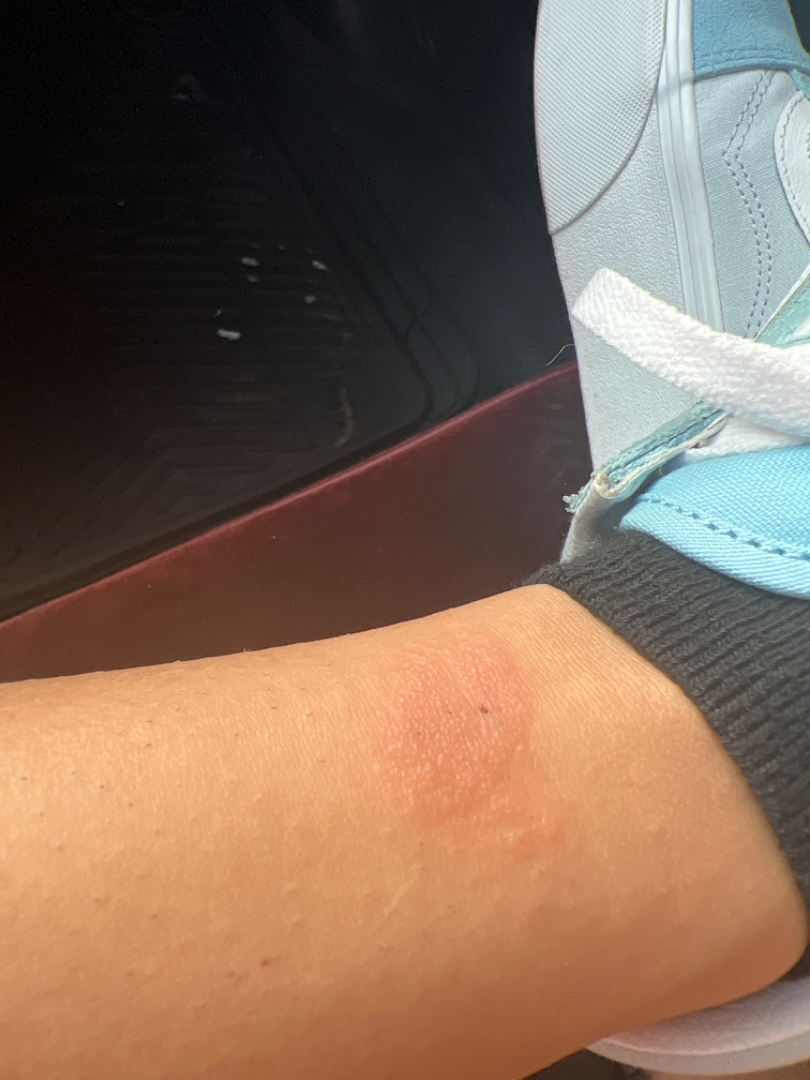image framing = at a distance, location = leg, assessment = favoring Insect Bite; with consideration of SK/ISK; the differential also includes Eczema.